Lay graders estimated a Monk skin tone scale of 2 · this image was taken at an angle.
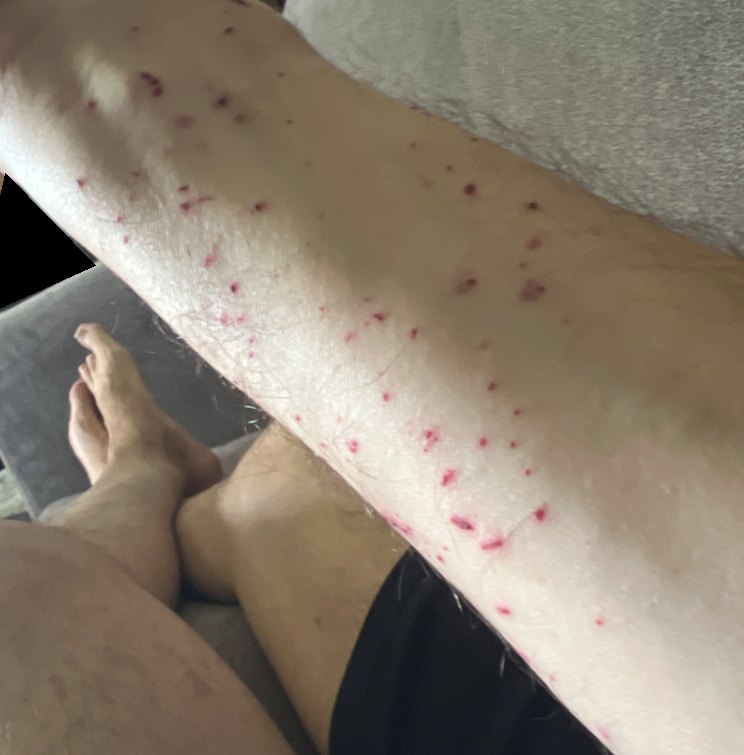assessment = not assessable